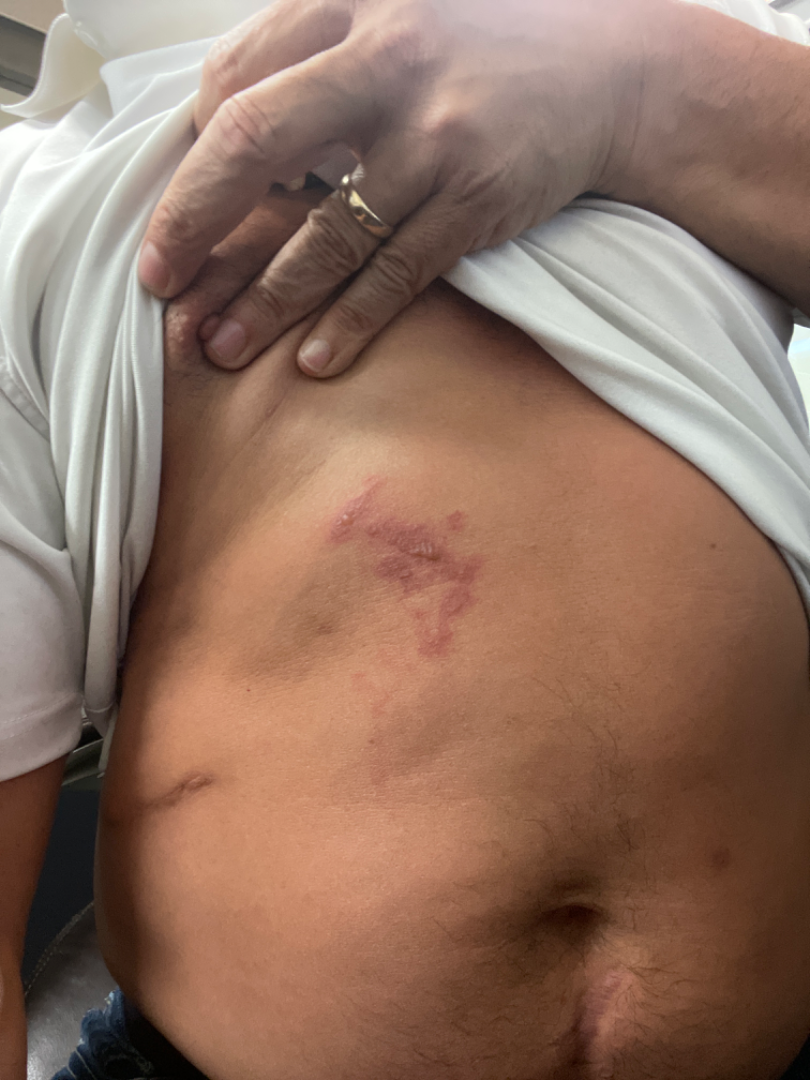skin tone: Fitzpatrick skin type IV | self-categorized as: a rash | contributor: male | history: about one day | shot type: at a distance | patient-reported symptoms: bothersome appearance, pain and burning | location: front of the torso | lesion texture: flat, raised or bumpy and fluid-filled | differential: the favored diagnosis is Allergic Contact Dermatitis.